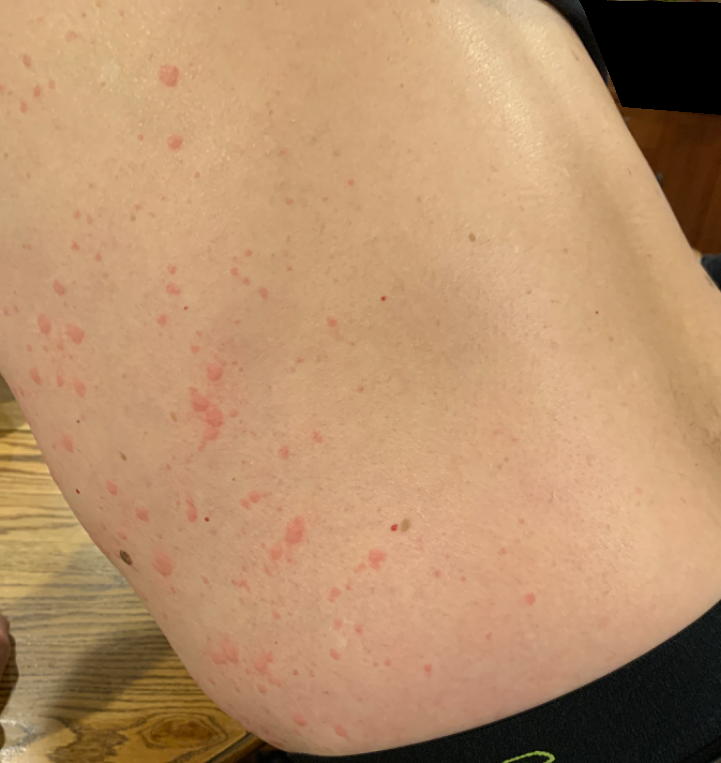This image was taken at a distance. Male patient, age 60–69. Symptoms reported: itching. The lesion involves the front of the torso. The patient described the issue as a rash. The reviewing dermatologist's impression was: most consistent with Urticaria.